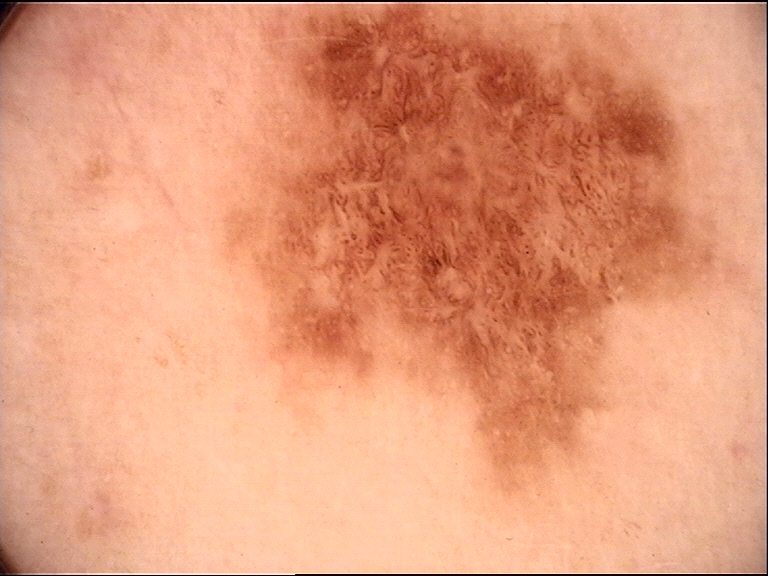Findings:
– class: dysplastic junctional nevus (expert consensus)